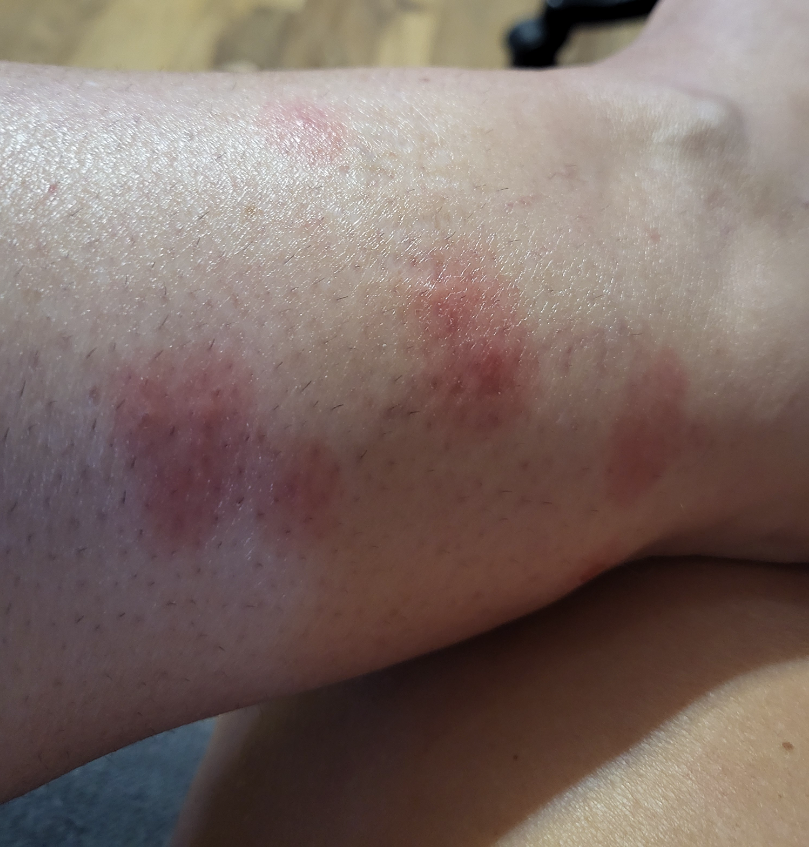Close-up view. Skin tone: Fitzpatrick skin type IV; lay graders estimated Monk Skin Tone 1 (US pool) or 2 (India pool). On photographic review by a dermatologist, Insect Bite (100%).